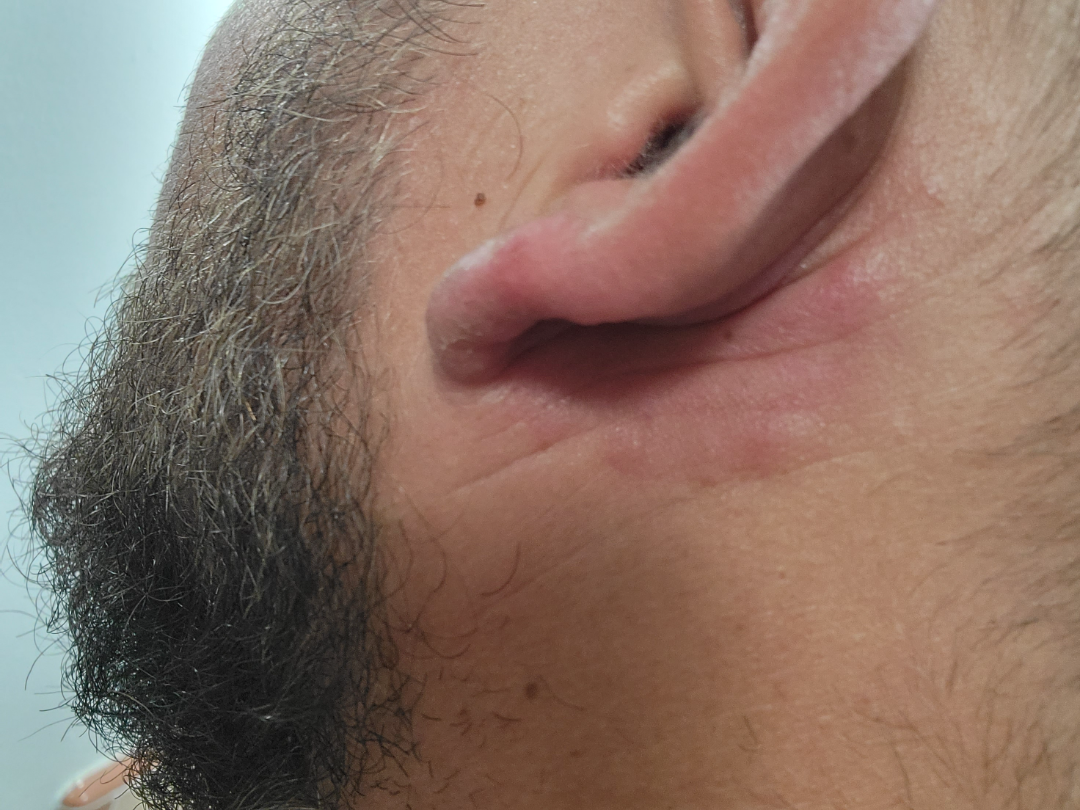<summary>
  <symptoms>darkening</symptoms>
  <skin_tone>
    <fitzpatrick>IV</fitzpatrick>
  </skin_tone>
  <shot_type>close-up</shot_type>
  <body_site>head or neck</body_site>
  <duration>one to four weeks</duration>
  <patient_category>a rash</patient_category>
  <differential>
    <tied_lead>Allergic Contact Dermatitis, Granulomatous disorder of the skin and subcutaneous tissue</tied_lead>
  </differential>
</summary>